A dermoscopic photograph of a skin lesion:
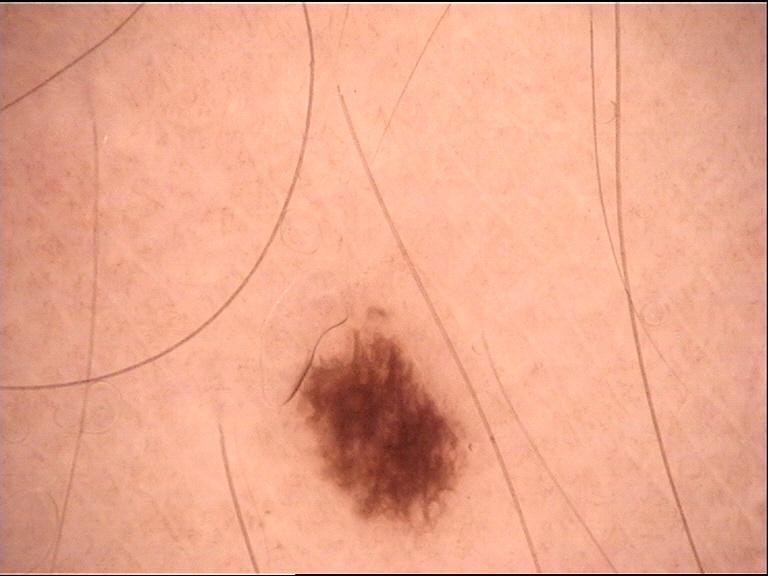The diagnosis was a dysplastic junctional nevus.